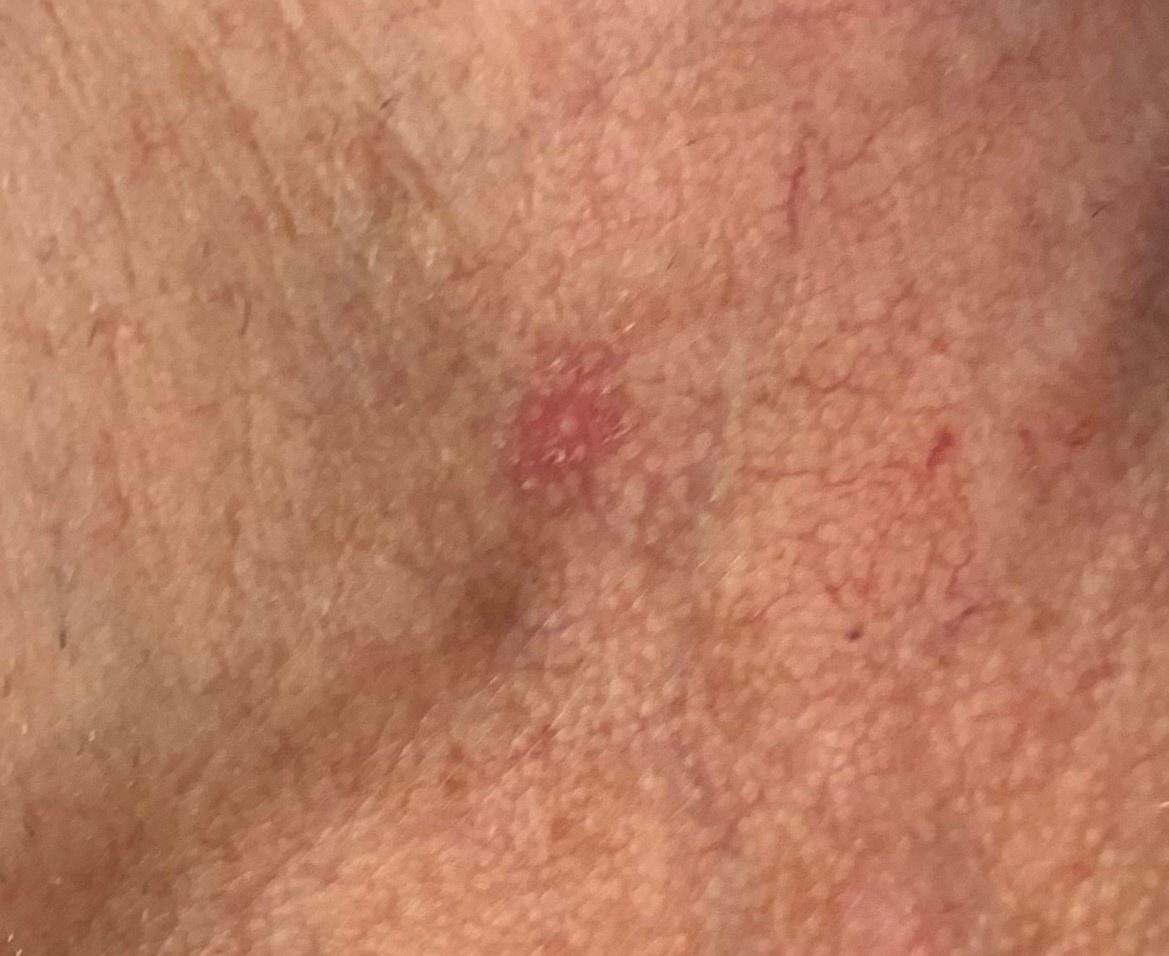Summary: A male patient roughly 70 years of age. A clinical photograph of a skin lesion. The lesion involves the head or neck. Pathology: The biopsy diagnosis was a basal cell carcinoma.